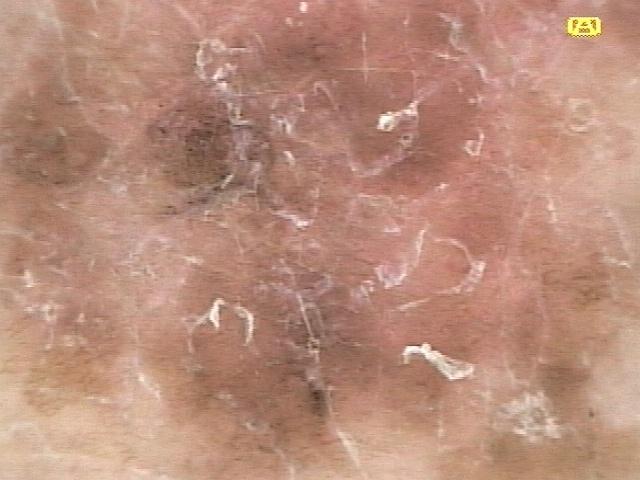Case summary:
The chart notes a prior melanoma but no melanoma in first-degree relatives. A dermoscopic image of a skin lesion. The lesion was found on a lower extremity.
Diagnosis:
Confirmed on histopathology as a skin cancer — a melanoma.